A female subject aged 60; a dermoscopic image of a skin lesion; collected as part of a research study, without a referral diagnosis.
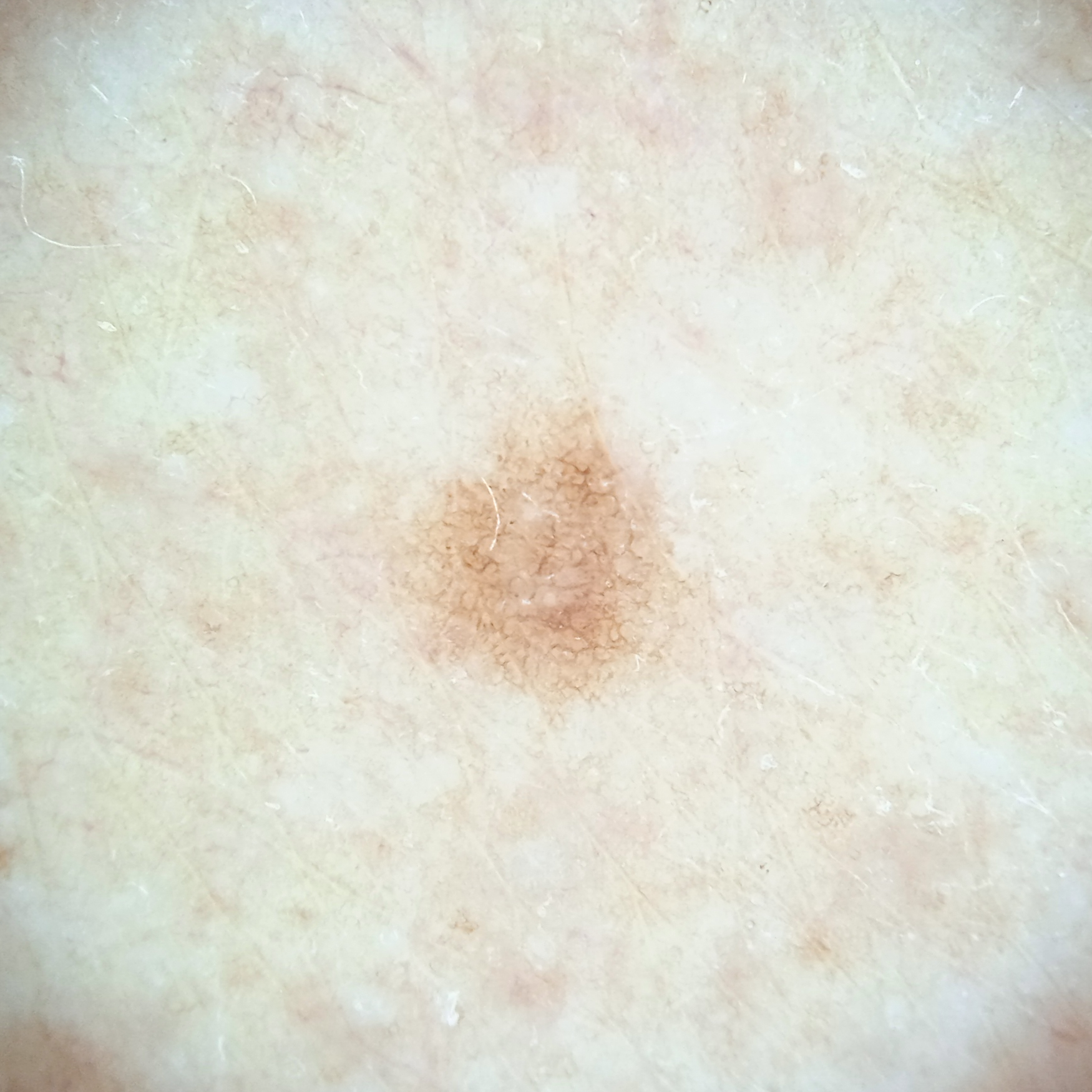Findings: The lesion measures approximately 2.8 mm. Assessment: Dermatologist review favored a melanocytic nevus.